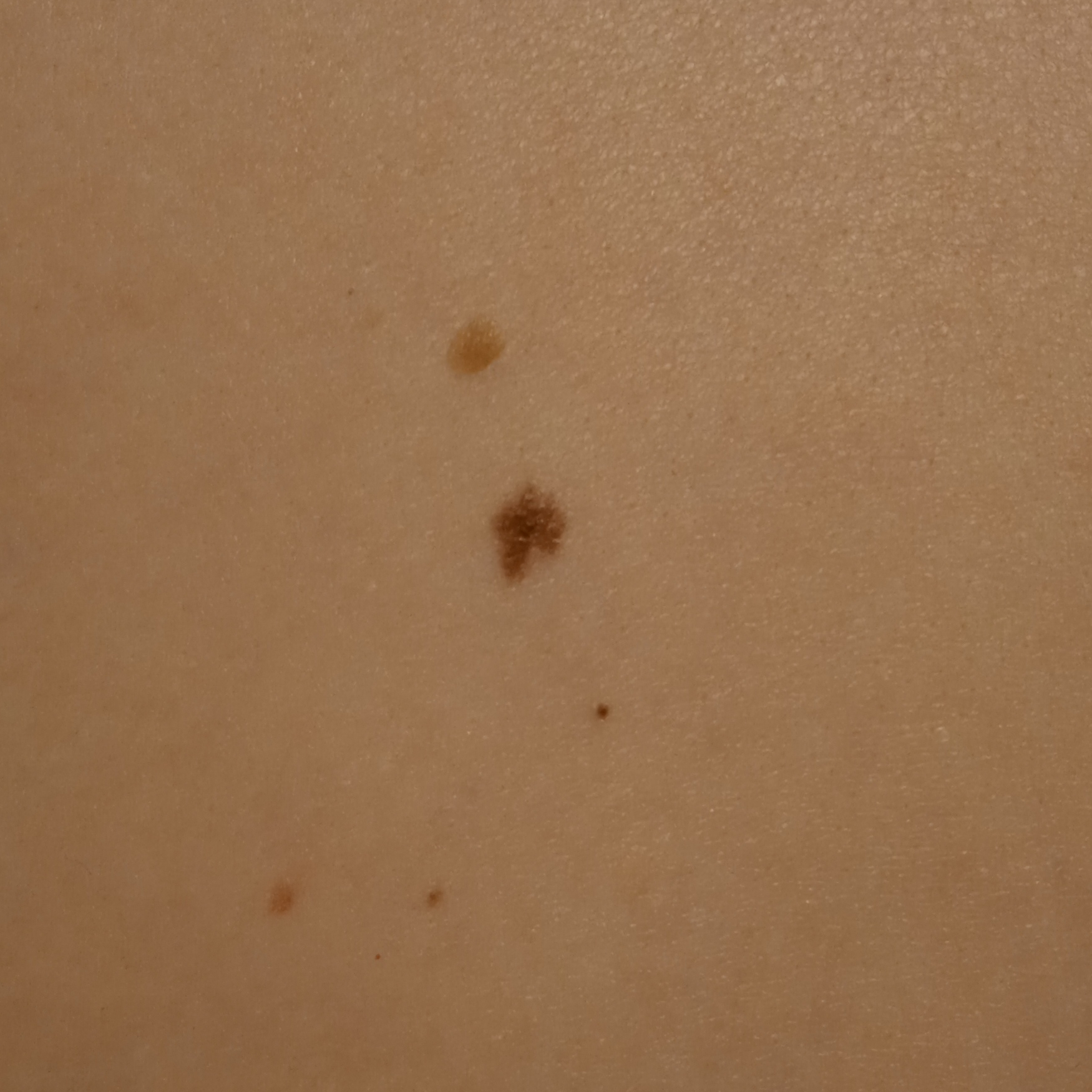image type: clinical photo | clinical context: research study (no referral diagnosis) | subject: female, age 27 | anatomic site: the back | size: 5.9 mm | diagnosis: melanocytic nevus (dermatologist consensus).